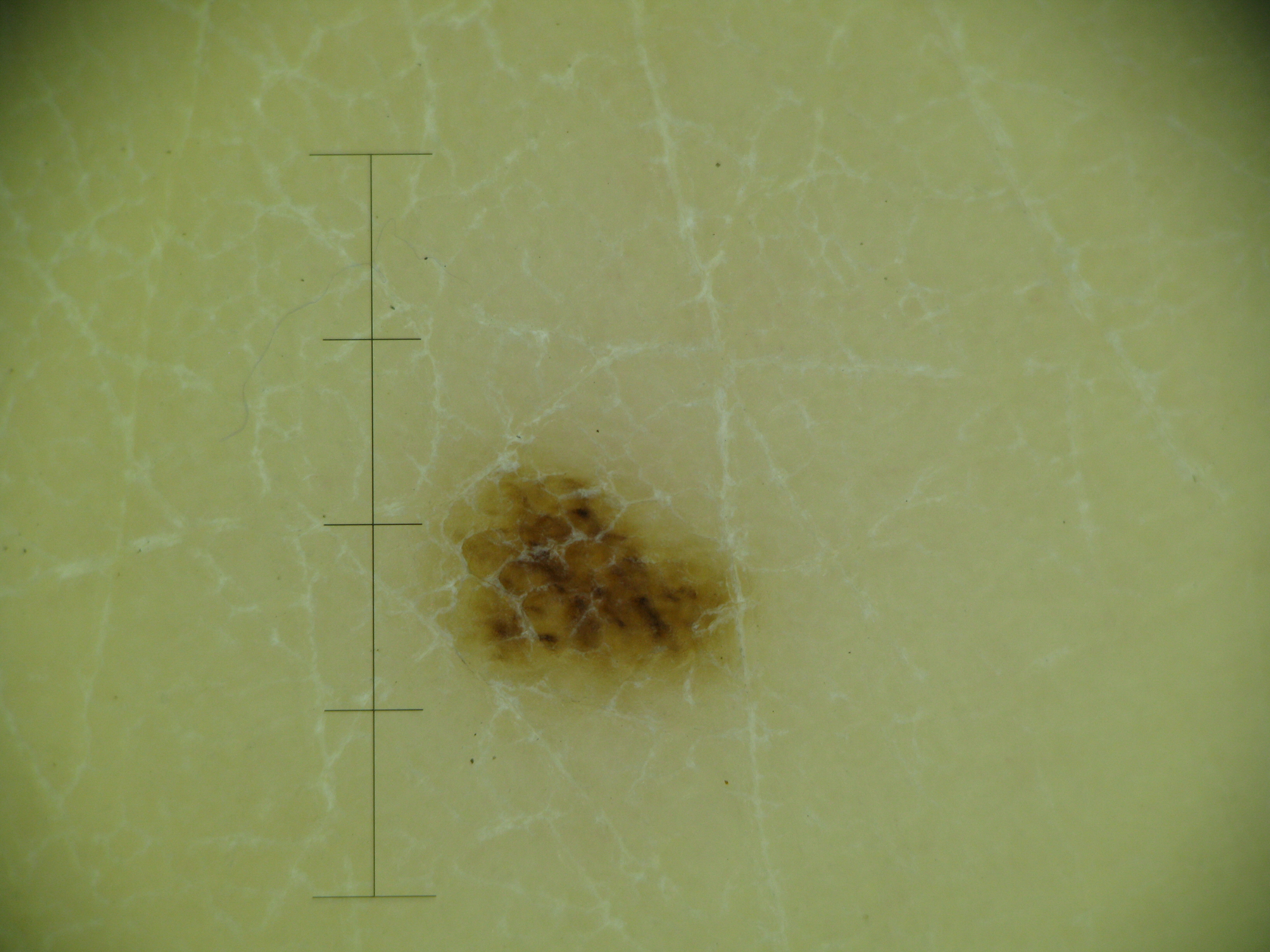modality — dermoscopy | assessment — acral dysplastic junctional nevus (expert consensus).